A dermatoscopic image of a skin lesion:
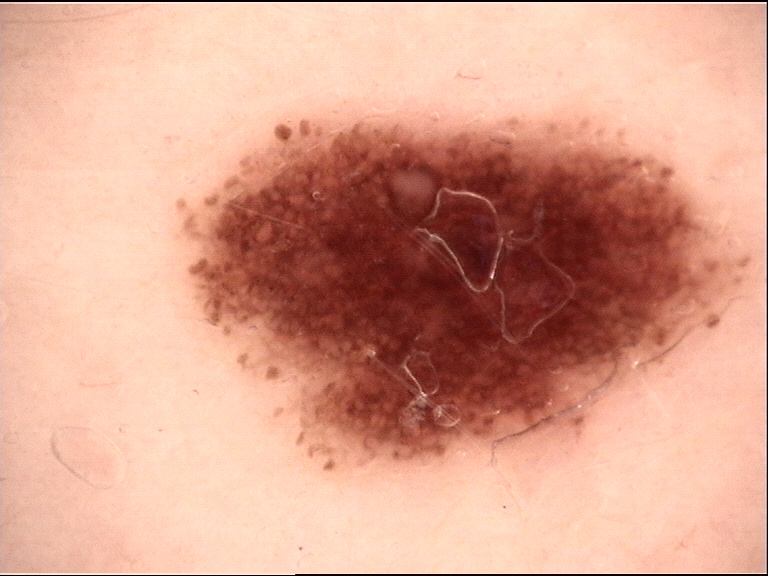Q: What was the diagnostic impression?
A: dysplastic junctional nevus (expert consensus)